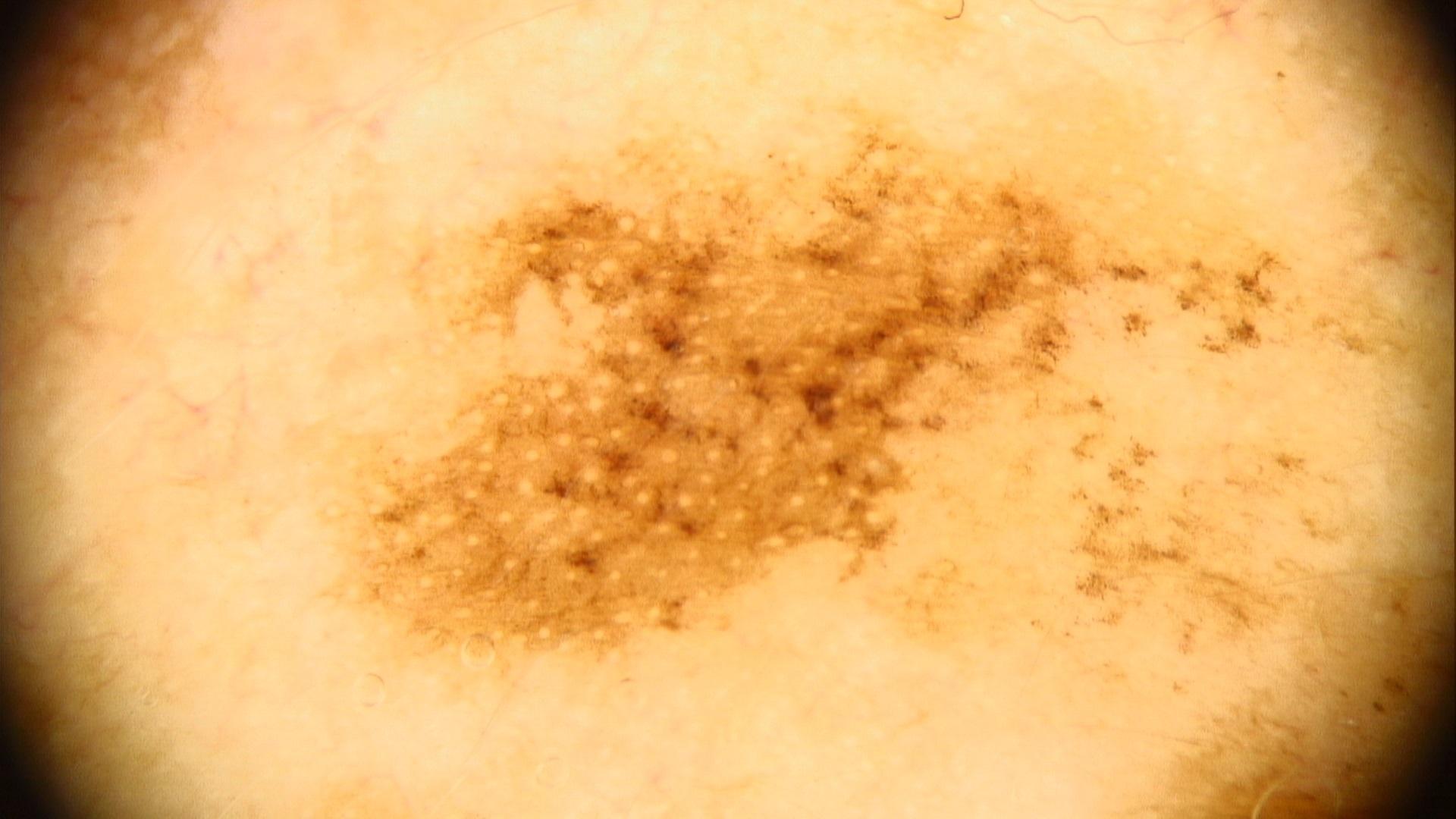Contact-polarized dermoscopy of a skin lesion. The lesion was found on the head or neck. Confirmed on histopathology as a melanoma.